A male patient, about 60 years old; a dermoscopic view of a skin lesion:
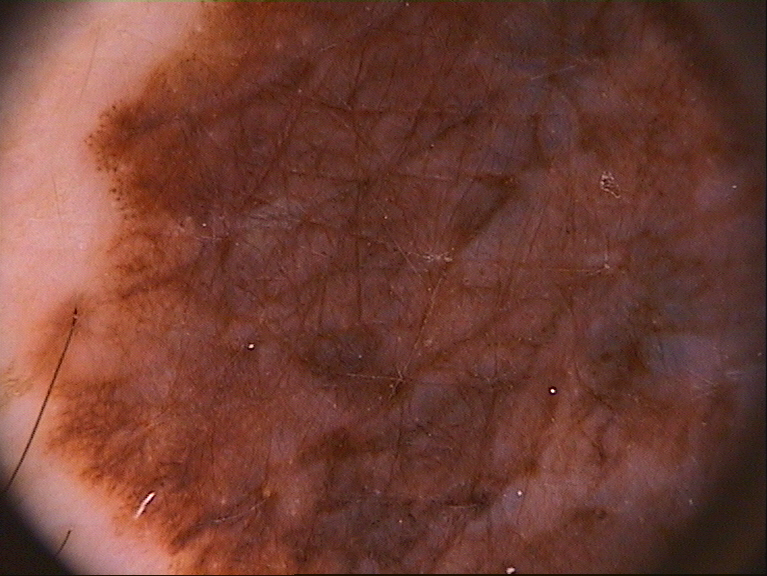Findings: Dermoscopic review identifies globules and pigment network; no streaks, negative network, or milia-like cysts. The lesion extends across almost the whole field of view. Pathology: The biopsy diagnosis was a melanoma, a malignant skin lesion.